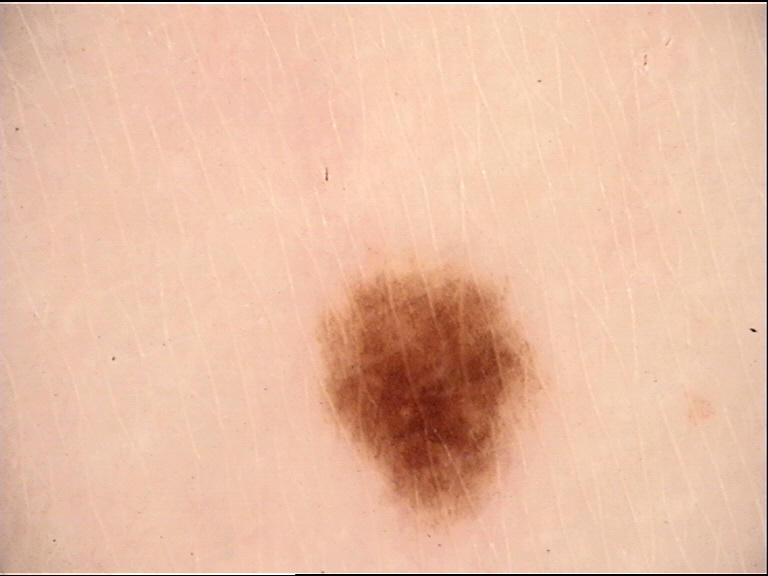Findings:
* image type: dermatoscopy
* class: junctional nevus (expert consensus)